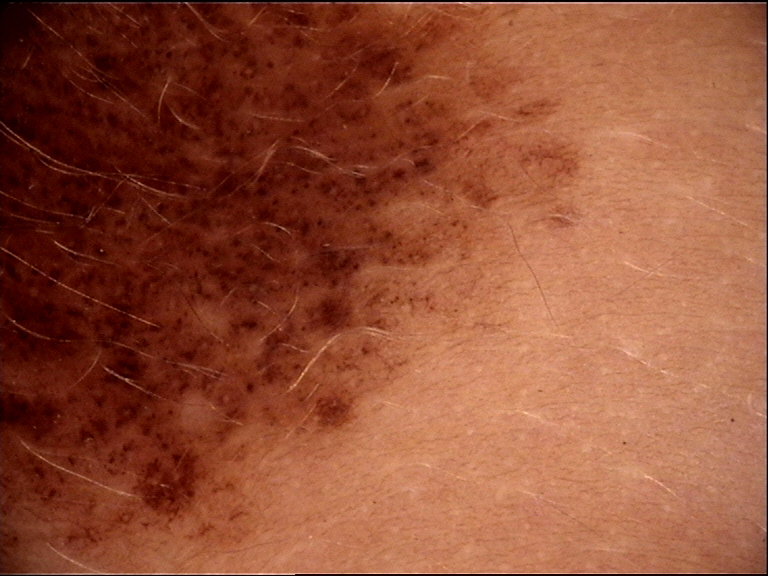| feature | finding |
|---|---|
| image | dermoscopy |
| diagnosis | congenital compound nevus (expert consensus) |